A female patient aged approximately 55 · a skin lesion imaged with a dermatoscope:
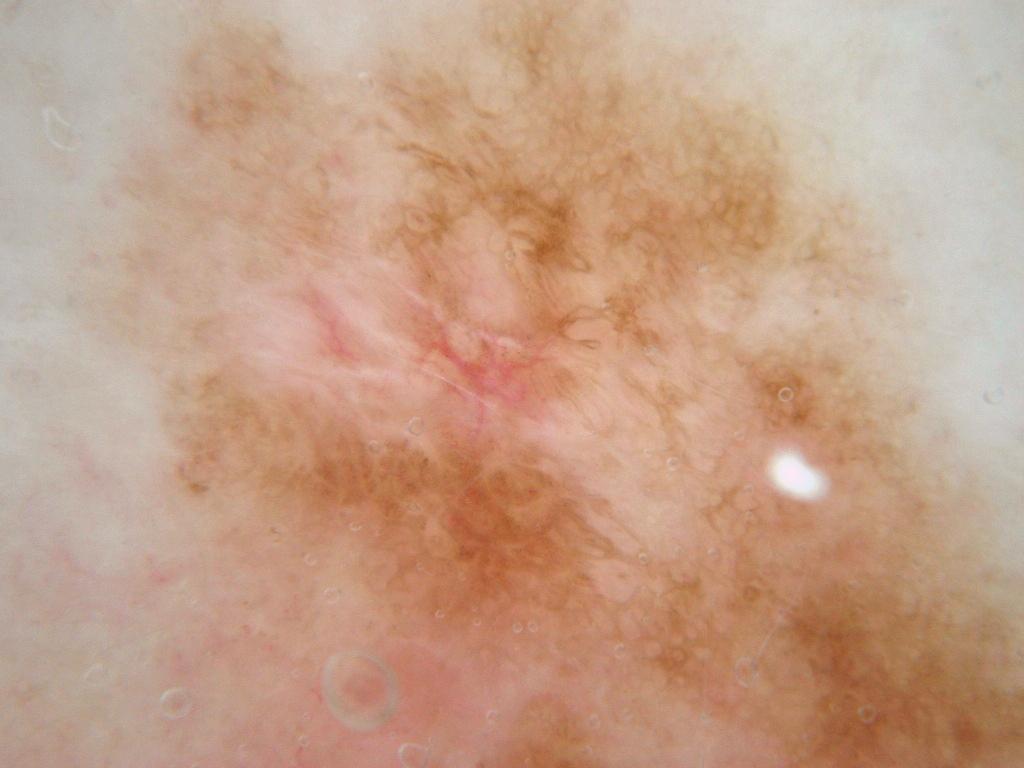The dermoscopic pattern shows milia-like cysts and pigment network; no streaks or negative network.
The lesion extends across almost the whole field of view.
The diagnostic assessment was a melanocytic nevus.